A dermoscopic photograph of a skin lesion.
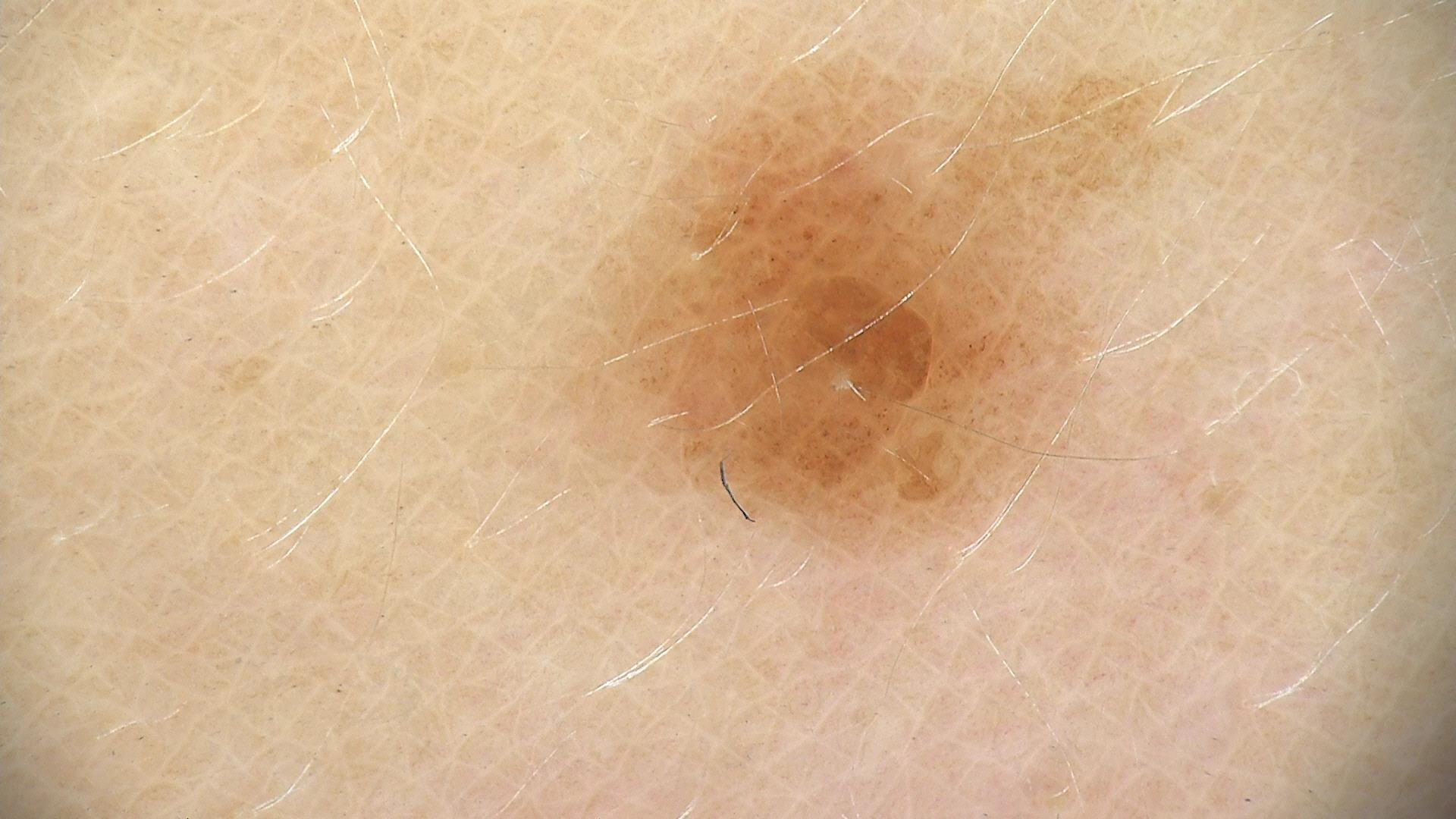Summary: The architecture is that of a banal lesion. Conclusion: The diagnosis was a compound nevus.